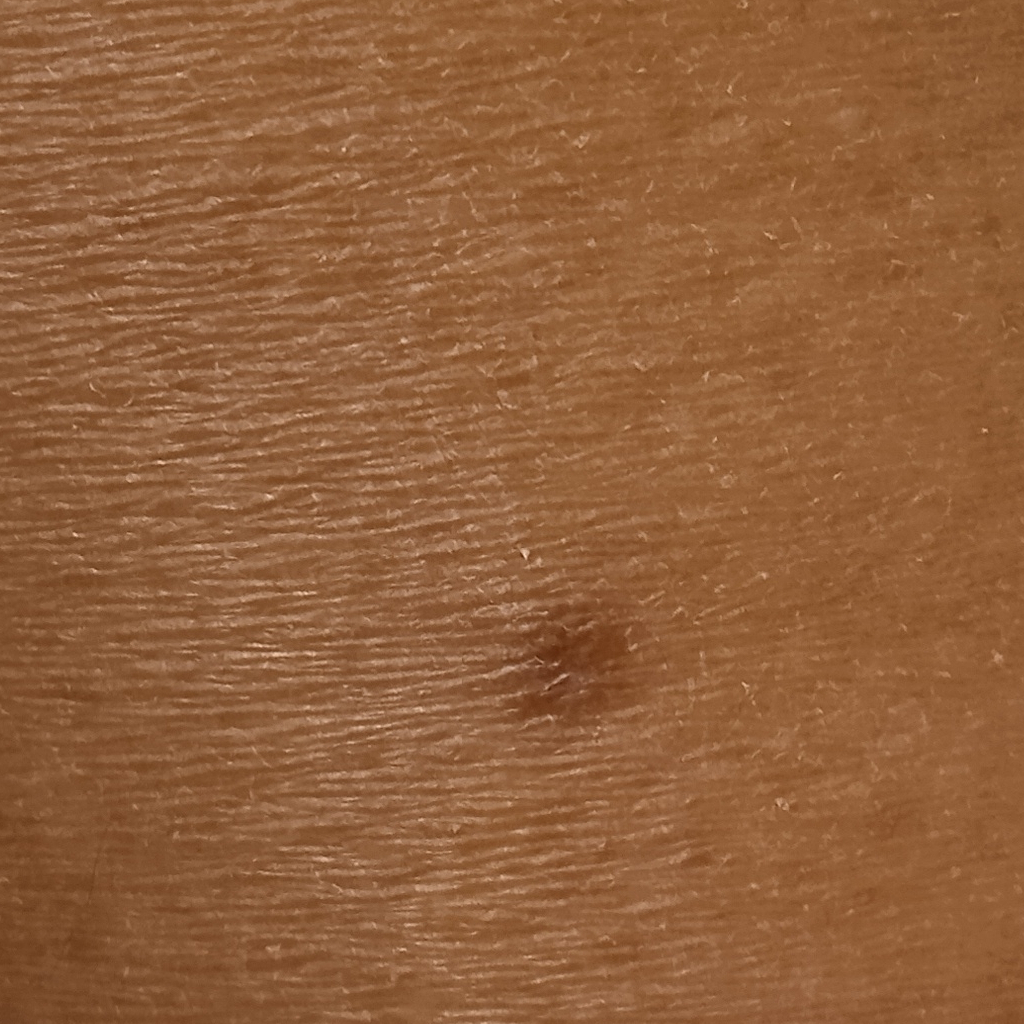image = clinical photograph | patient = female, 58 years old | clinical context = research study (no referral diagnosis) | size = 5.2 mm | assessment = dermatofibroma (dermatologist consensus).